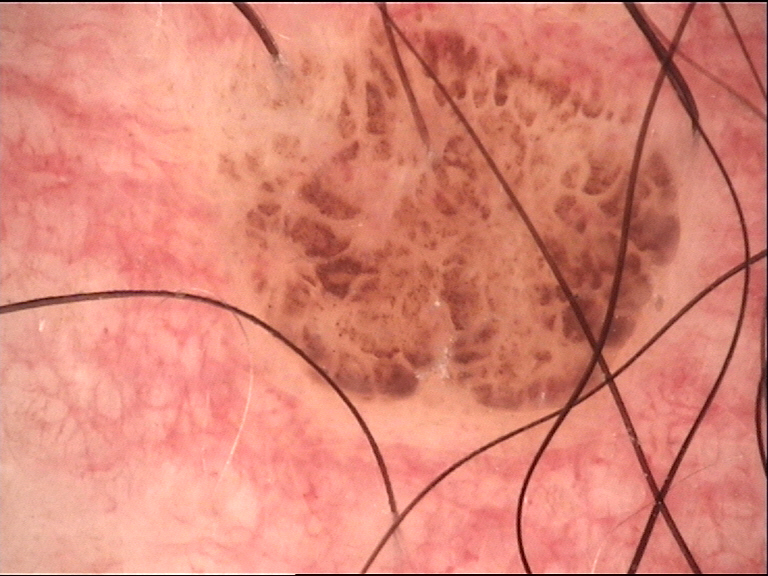Summary:
The architecture is that of a banal lesion.
Conclusion:
Labeled as a compound nevus.